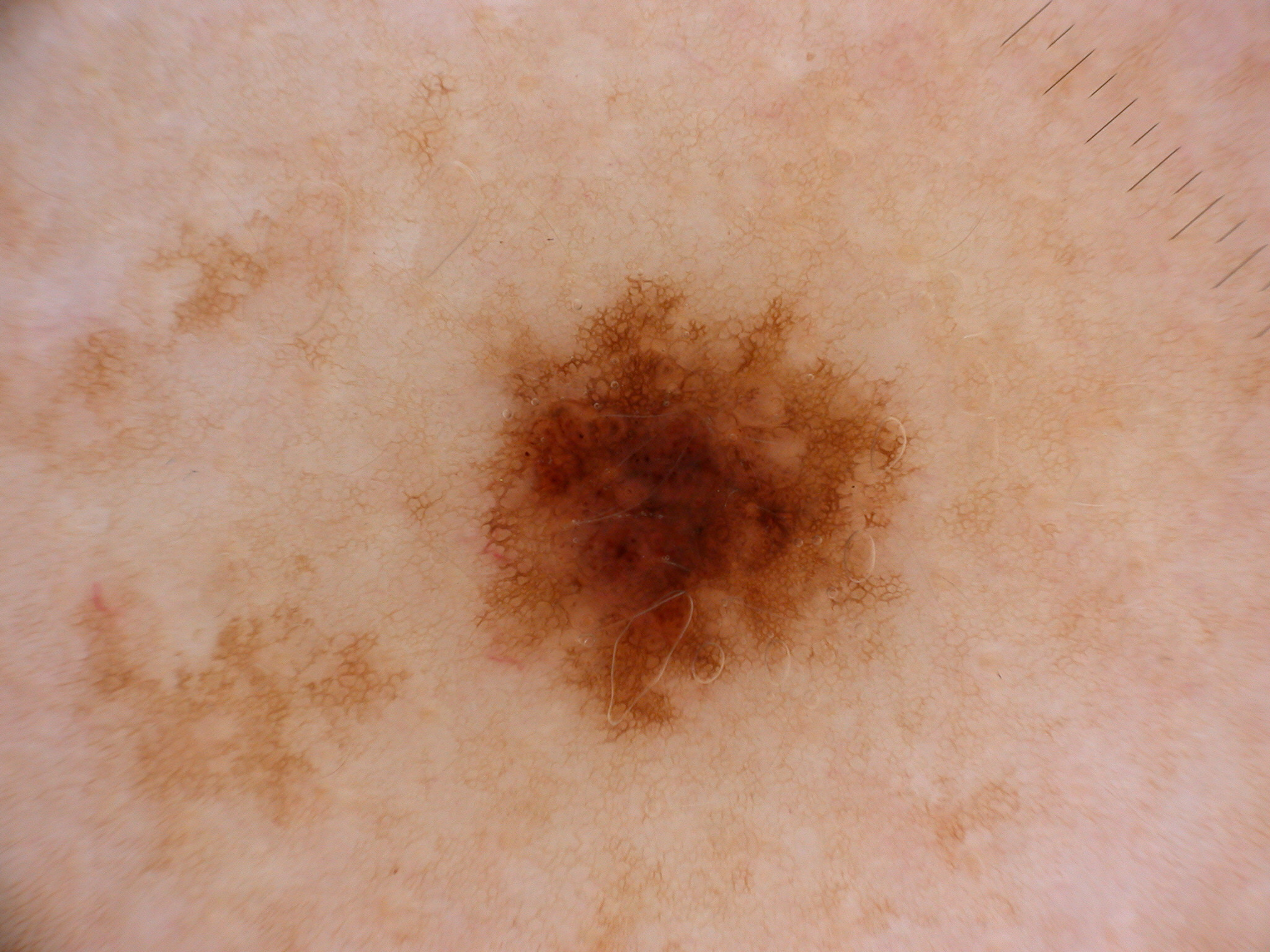Summary:
A dermoscopic close-up of a skin lesion. The lesion takes up a moderate portion of the field. Dermoscopic examination shows pigment network and globules. The lesion occupies the region 405 277 913 747.
Conclusion:
The clinical diagnosis was a melanocytic nevus, a benign lesion.